A skin lesion imaged with contact-polarized dermoscopy. A male subject approximately 40 years of age.
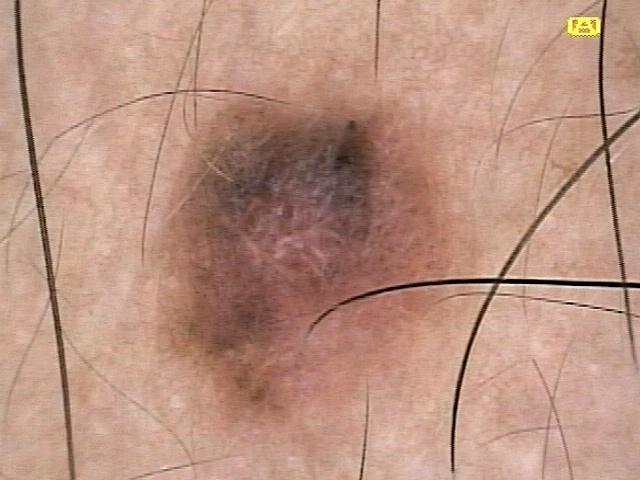body site: the head or neck | diagnosis: Melanoma (biopsy-proven).